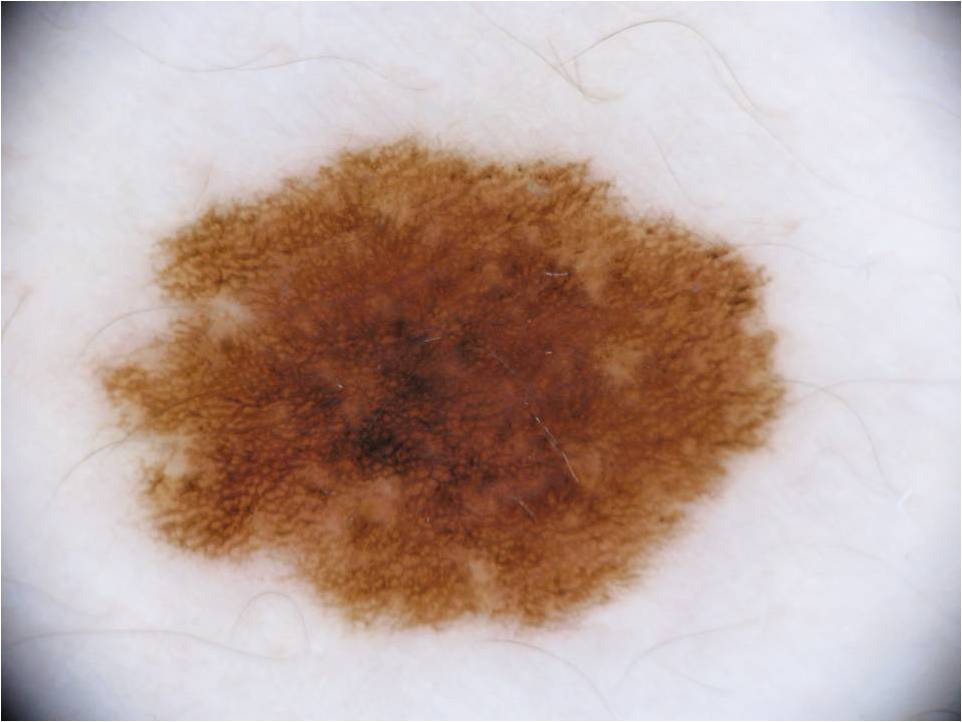patient=female, aged approximately 35
modality=dermoscopy of a skin lesion
dermoscopic features=pigment network; absent: negative network, streaks, globules, and milia-like cysts
location=92 131 785 630
lesion extent=large
diagnostic label=a melanocytic nevus, a benign skin lesion